Dermoscopy of a skin lesion.
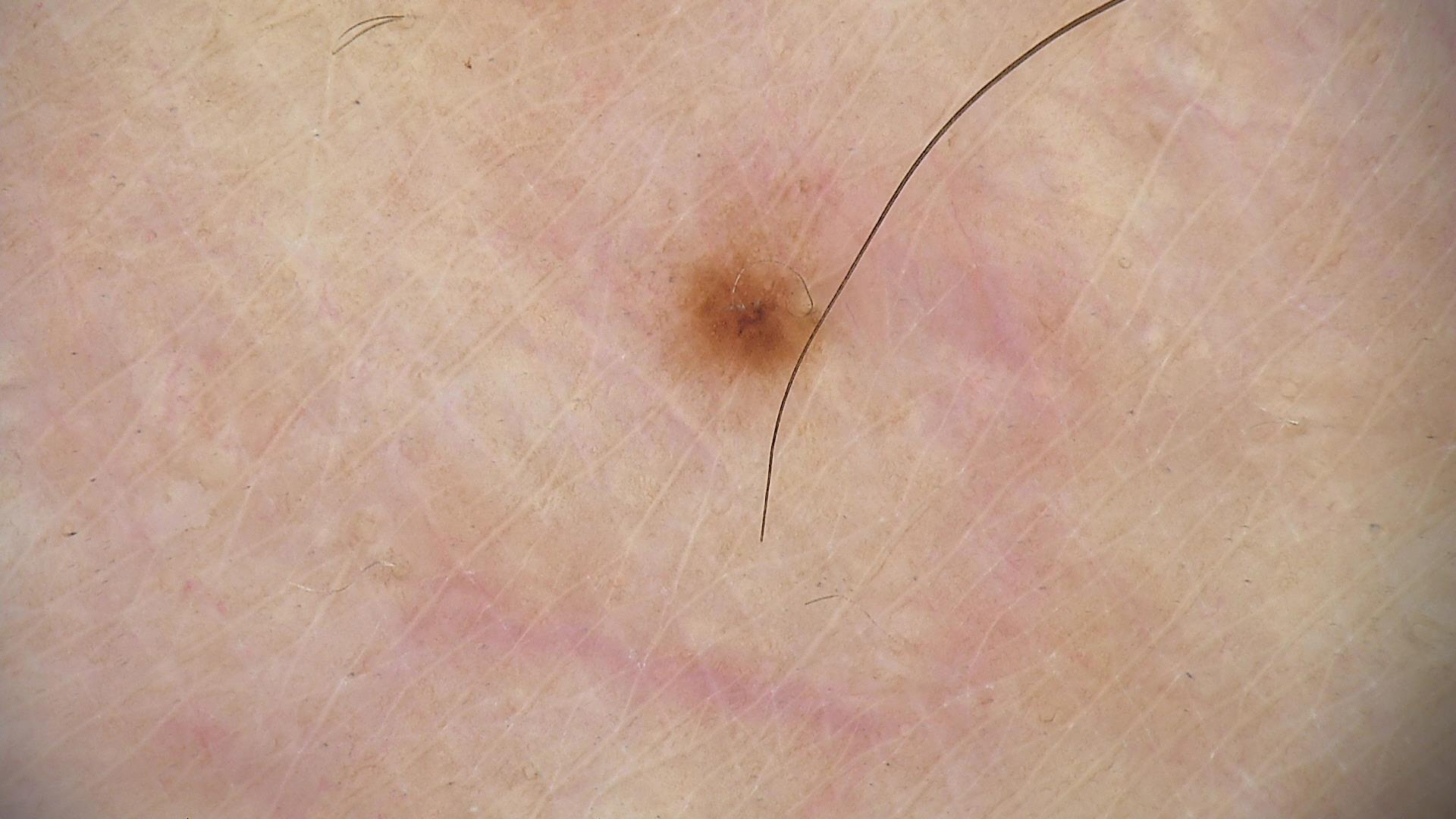Impression:
Classified as a dysplastic junctional nevus.